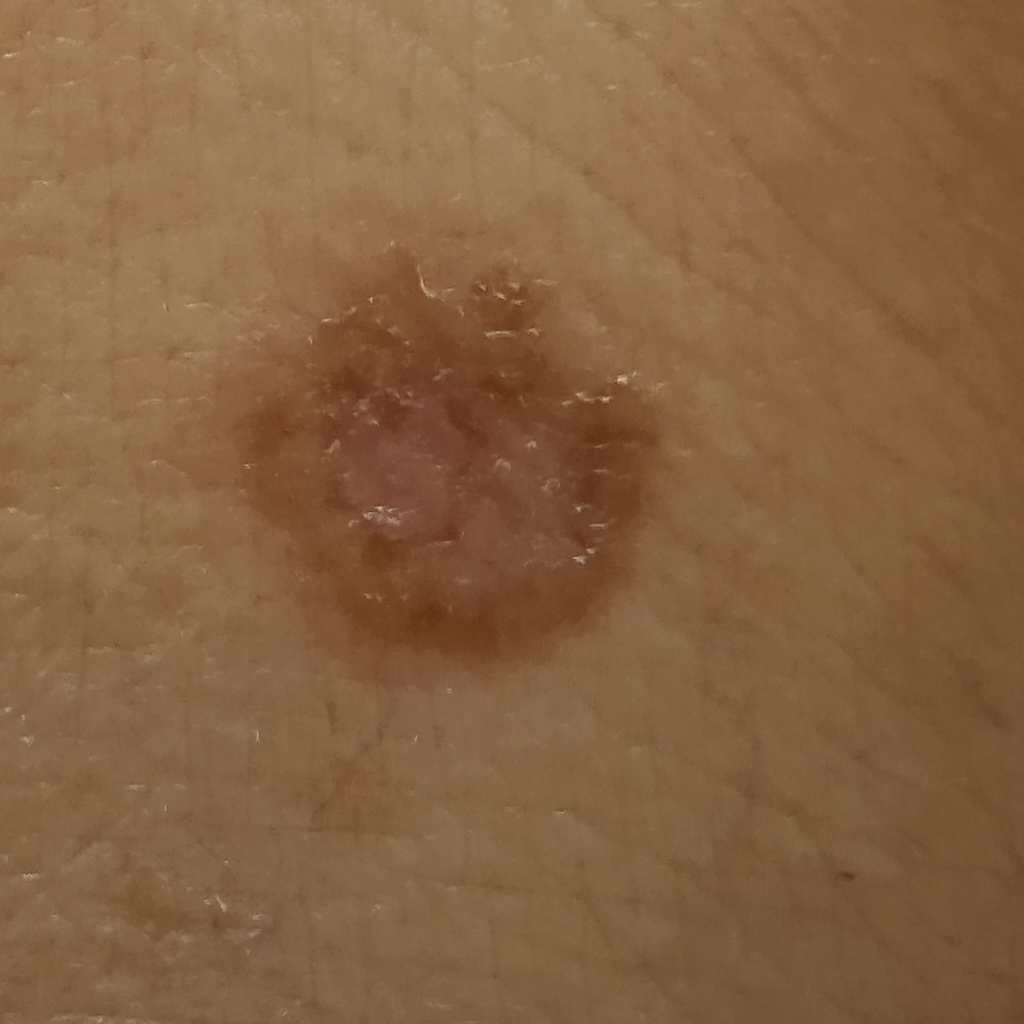Case:
- referral context · clinical suspicion of basal cell carcinoma
- sun reaction · skin tans without first burning
- nevus count · few melanocytic nevi overall
- risk factors · a personal history of skin cancer, a personal history of cancer
- patient · female, 60 years of age
- lesion size · 13.2 mm
- diagnostic label · basal cell carcinoma (dermatologist consensus)